A dermoscopy image of a single skin lesion.
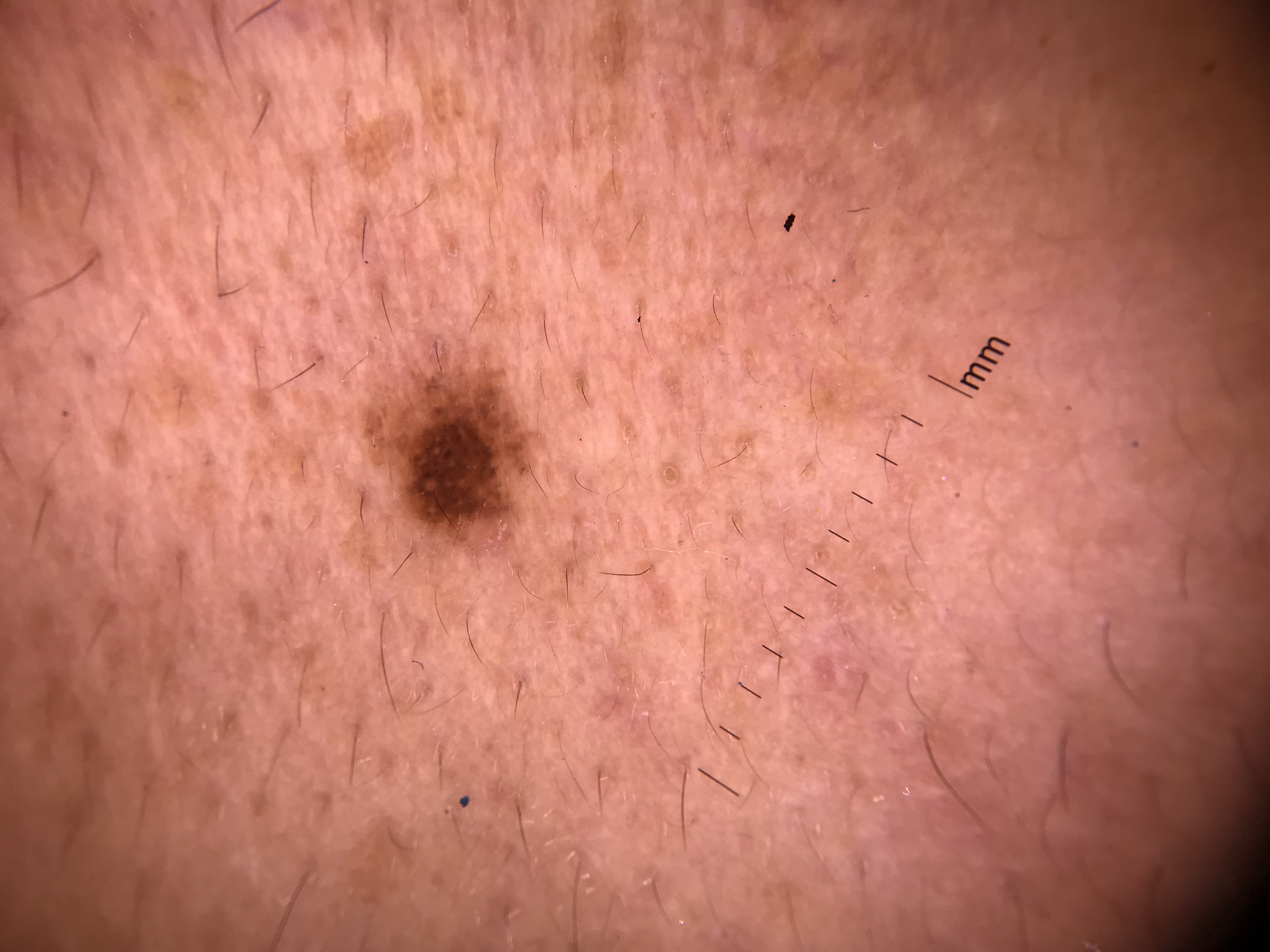This is a banal lesion.
Consistent with a junctional nevus.